The affected area is the leg and arm · the photograph was taken at a distance — 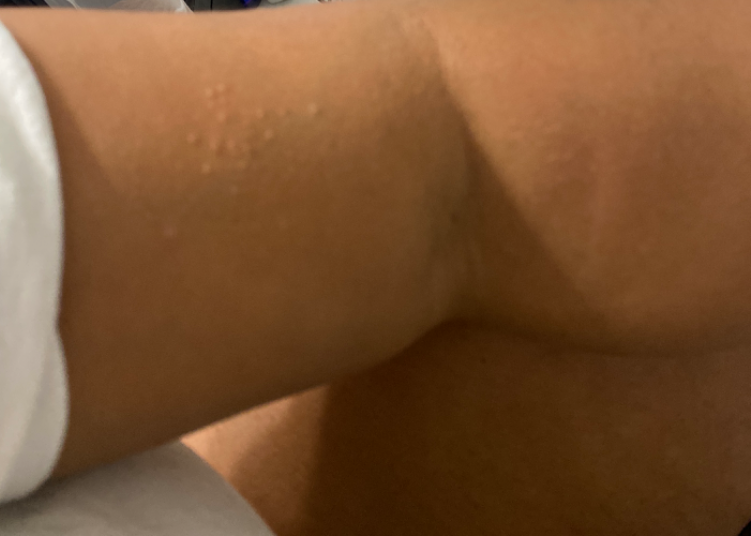History: The lesion is associated with itching and bothersome appearance. FST III. The patient considered this a rash. No associated systemic symptoms reported. The condition has been present for less than one week. Impression: On dermatologist assessment of the image, most likely Folliculitis.